Dermoscopy of a skin lesion; a female subject, about 85 years old or older — 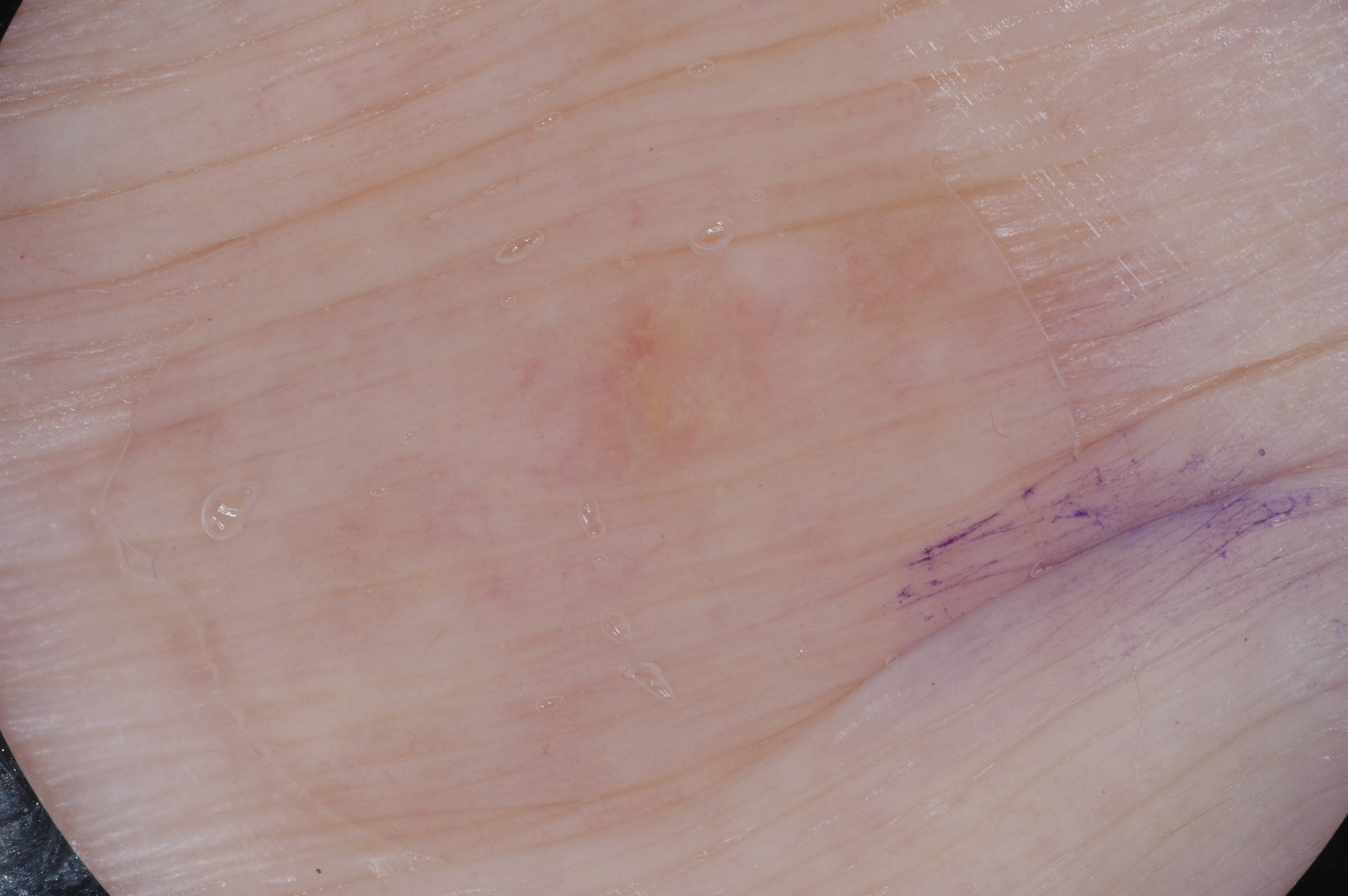The lesion is located at x1=497, y1=251, x2=837, y2=496. The lesion covers approximately 5% of the dermoscopic field. The dermoscopic pattern shows no pigment network, streaks, negative network, or milia-like cysts. Clinically diagnosed as a seborrheic keratosis, a lesion of keratinocytic origin.